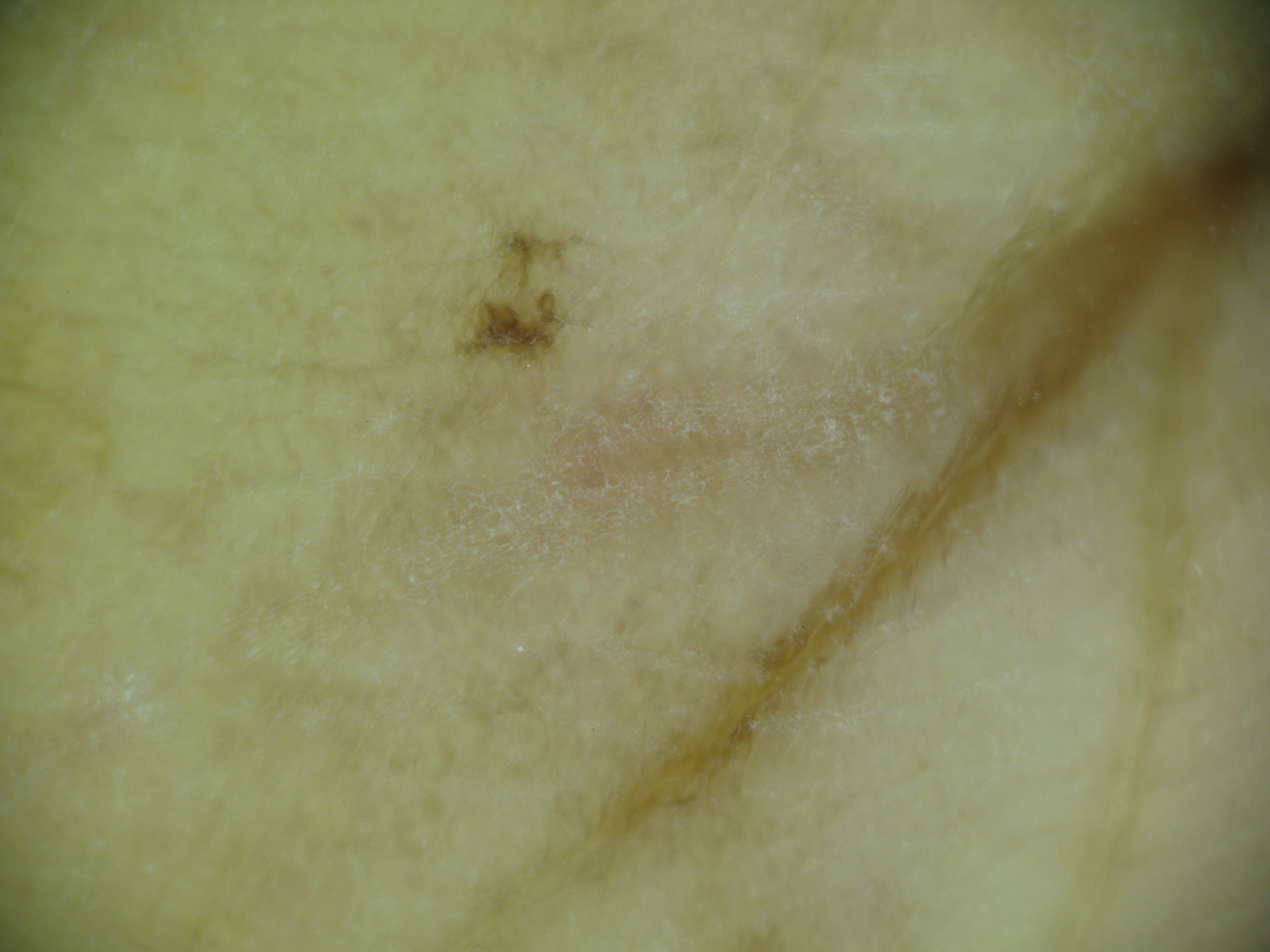<case>
  <image>dermoscopy</image>
  <diagnosis>
    <name>acral dysplastic junctional nevus</name>
    <code>ajd</code>
    <malignancy>benign</malignancy>
    <super_class>melanocytic</super_class>
    <confirmation>expert consensus</confirmation>
  </diagnosis>
</case>